An image taken at a distance, the lesion involves the arm and front of the torso: 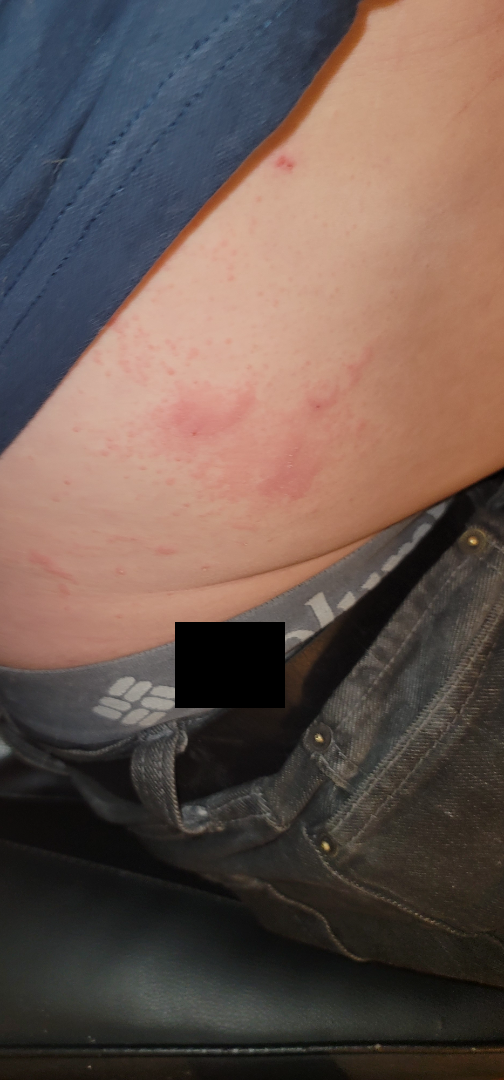On teledermatology review: Eczema (weight 0.54); Tinea (weight 0.23); Psoriasis (weight 0.23).